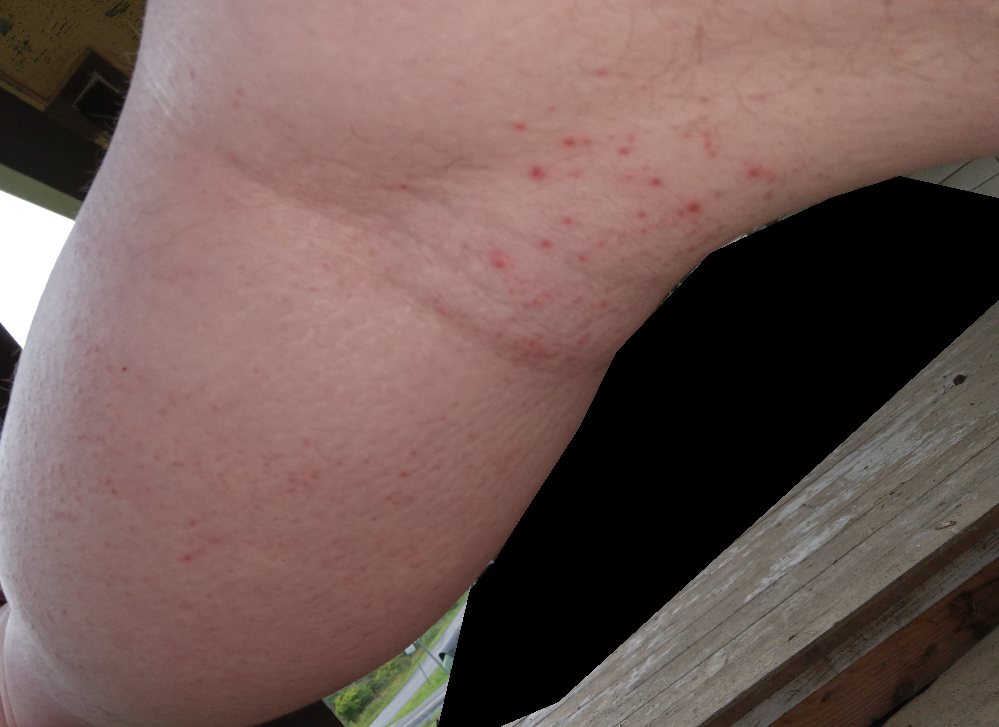Three dermatologists each reviewed the case: most consistent with Eczema; less likely is Folliculitis; less probable is Leukocytoclastic Vasculitis; a remote consideration is Pruritic dermatitis.